Located on the palm and arm · the photo was captured at an angle · reported duration is less than one week · the subject is 50–59, female · the patient indicates the lesion is raised or bumpy · the patient described the issue as skin that appeared healthy to them · reported lesion symptoms include burning and itching — 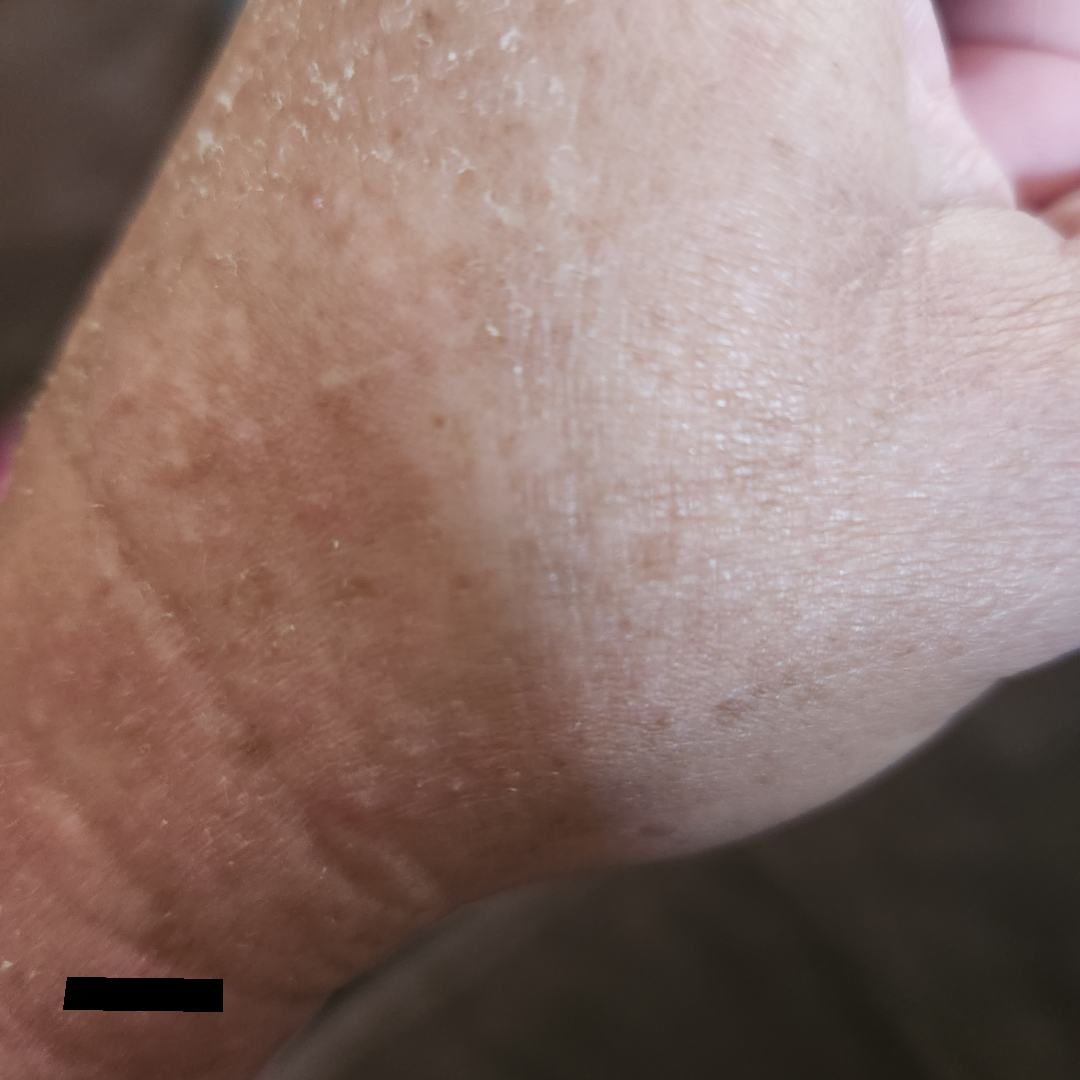Review:
The image was not sufficient for the reviewer to characterize the skin condition.